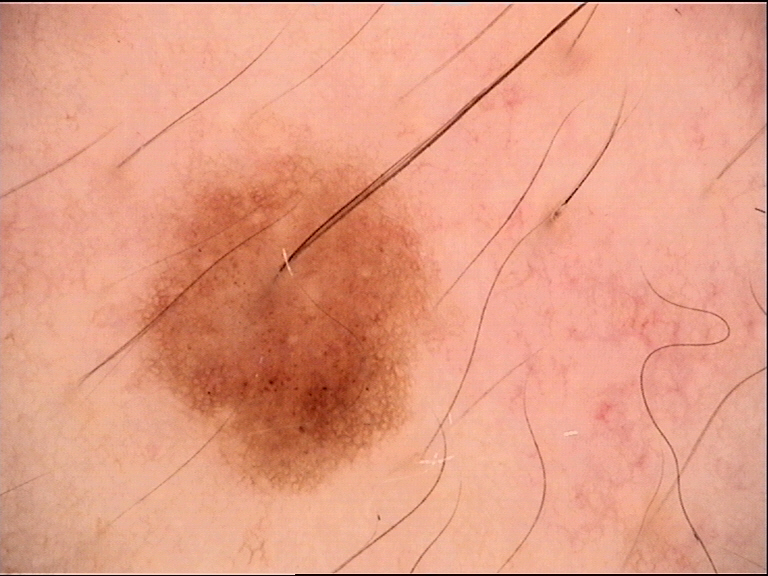– label · dysplastic junctional nevus (expert consensus)